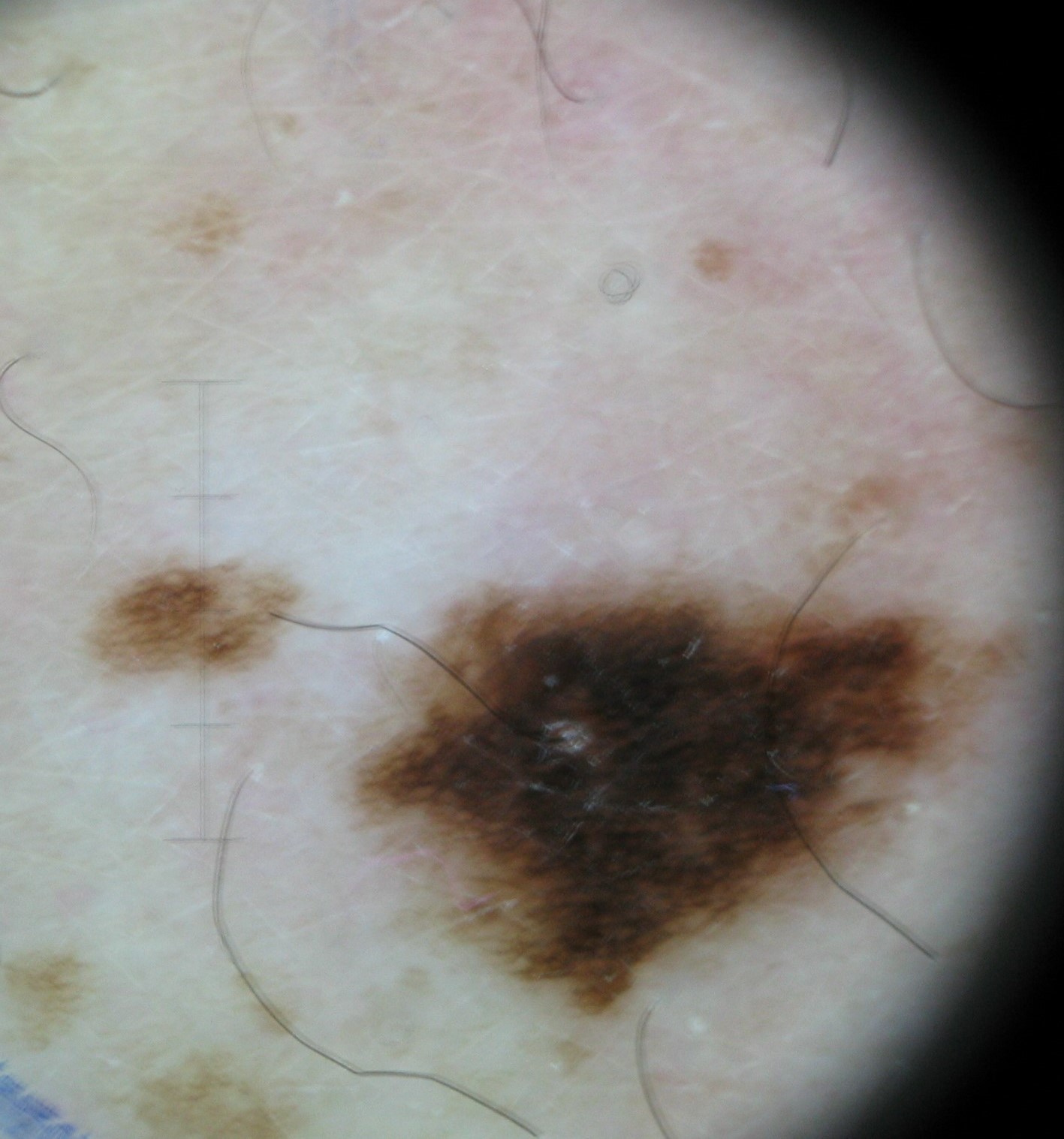| key | value |
|---|---|
| label | dysplastic compound nevus (expert consensus) |